Close-up view. Located on the leg. The contributor is 40–49, female:
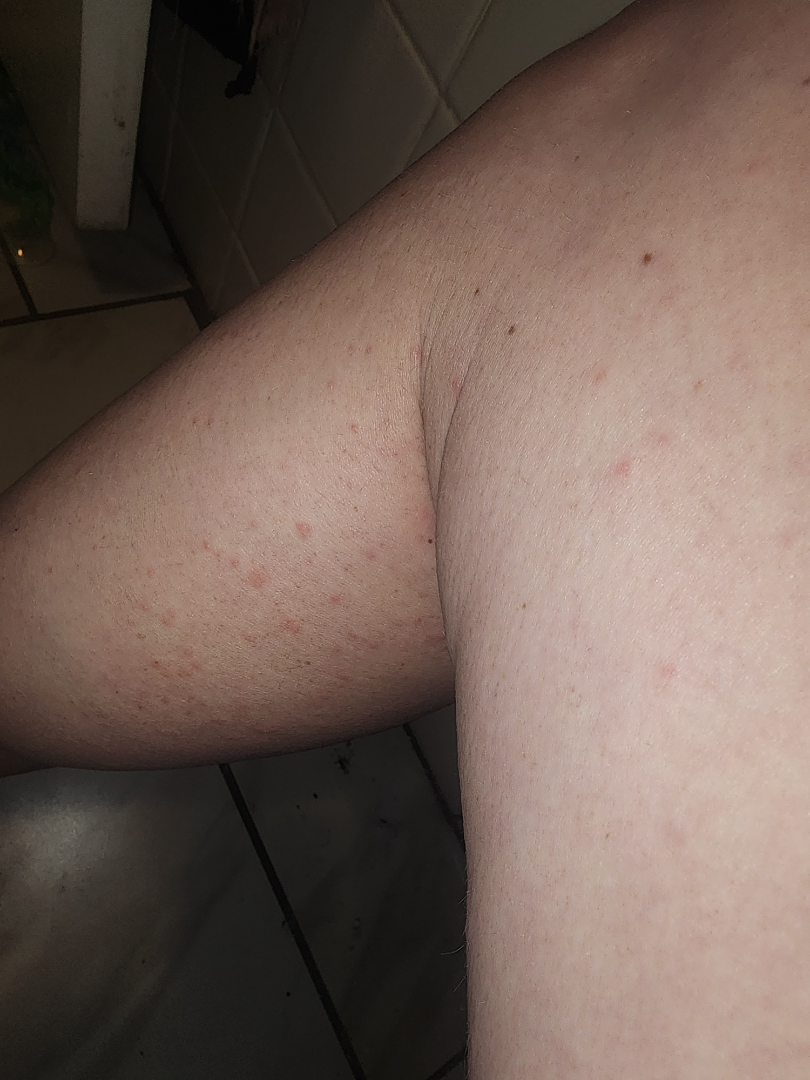Assessment:
The image was not sufficient for the reviewer to characterize the skin condition.